The subject is 50–59, female; an image taken at a distance; the affected area is the head or neck and front of the torso: 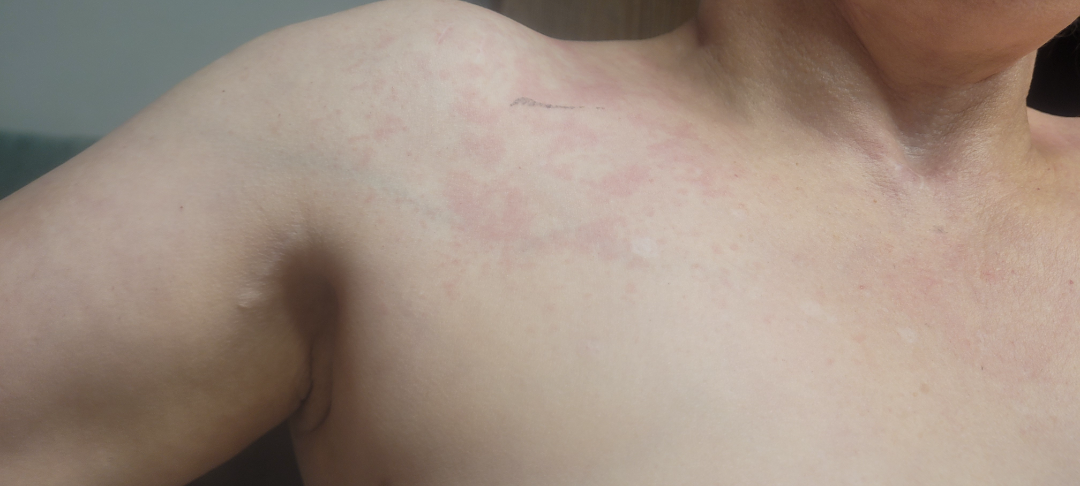assessment: indeterminate
duration: less than one week
patient_category: a rash
texture: flat